Acquired for a research image collection, with no referral diagnosis. A female patient aged 27. A macroscopic clinical photograph of a skin lesion. The patient says their skin reddens with sun exposure.
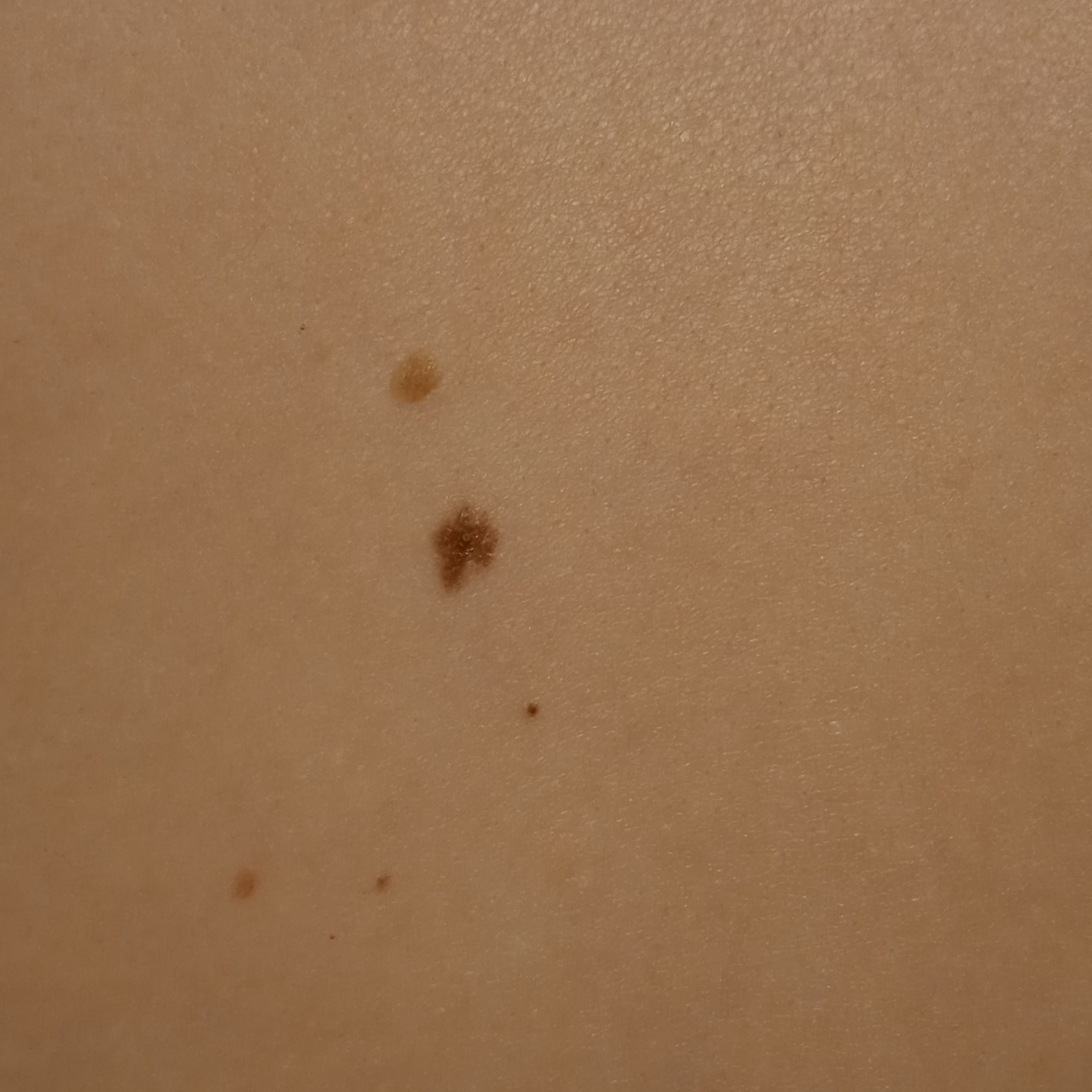The lesion is on the back. Measuring roughly 5.9 mm. Dermatologist review favored a melanocytic nevus.